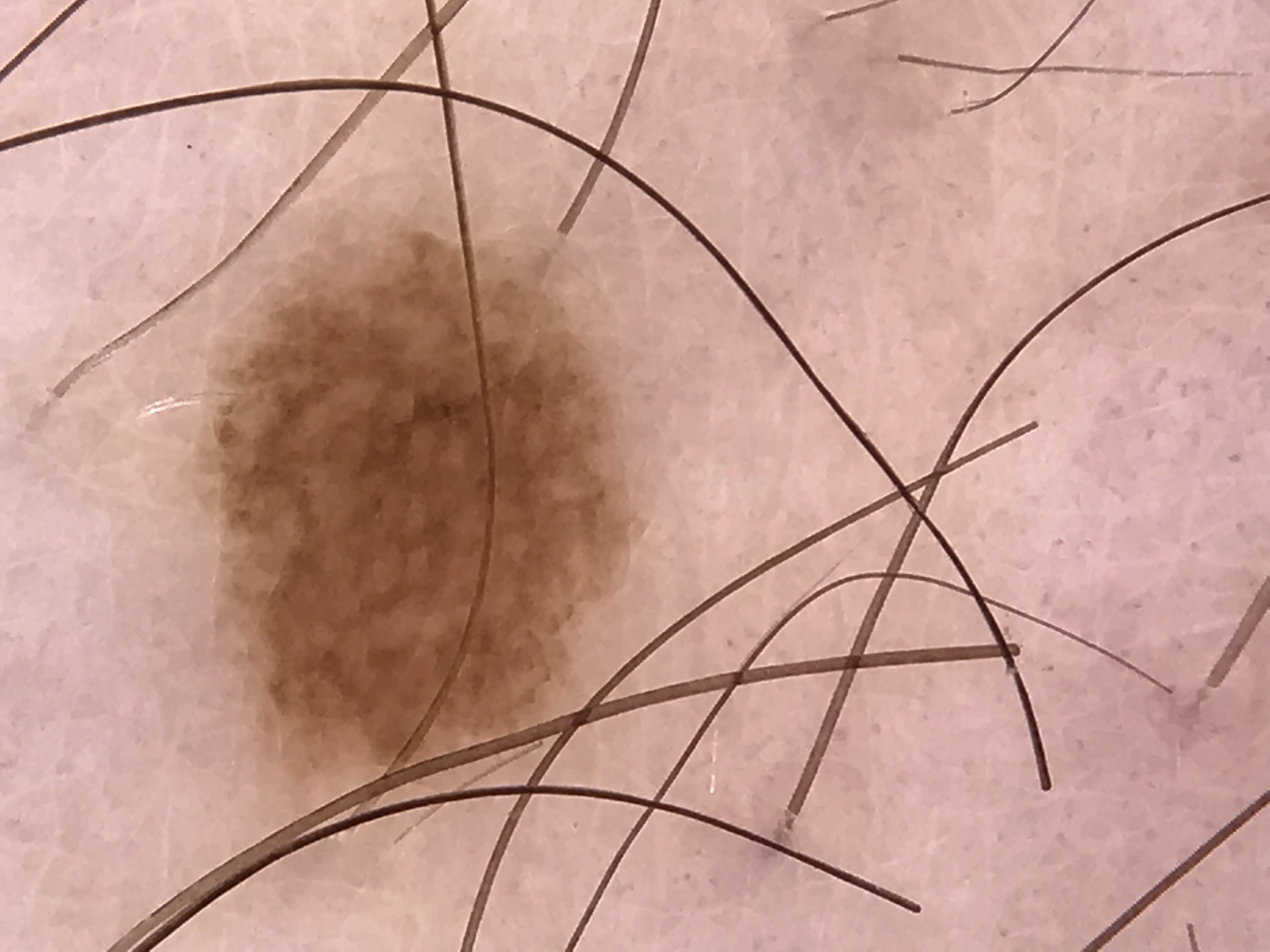modality=dermoscopy; category=banal; diagnosis=junctional nevus (expert consensus).